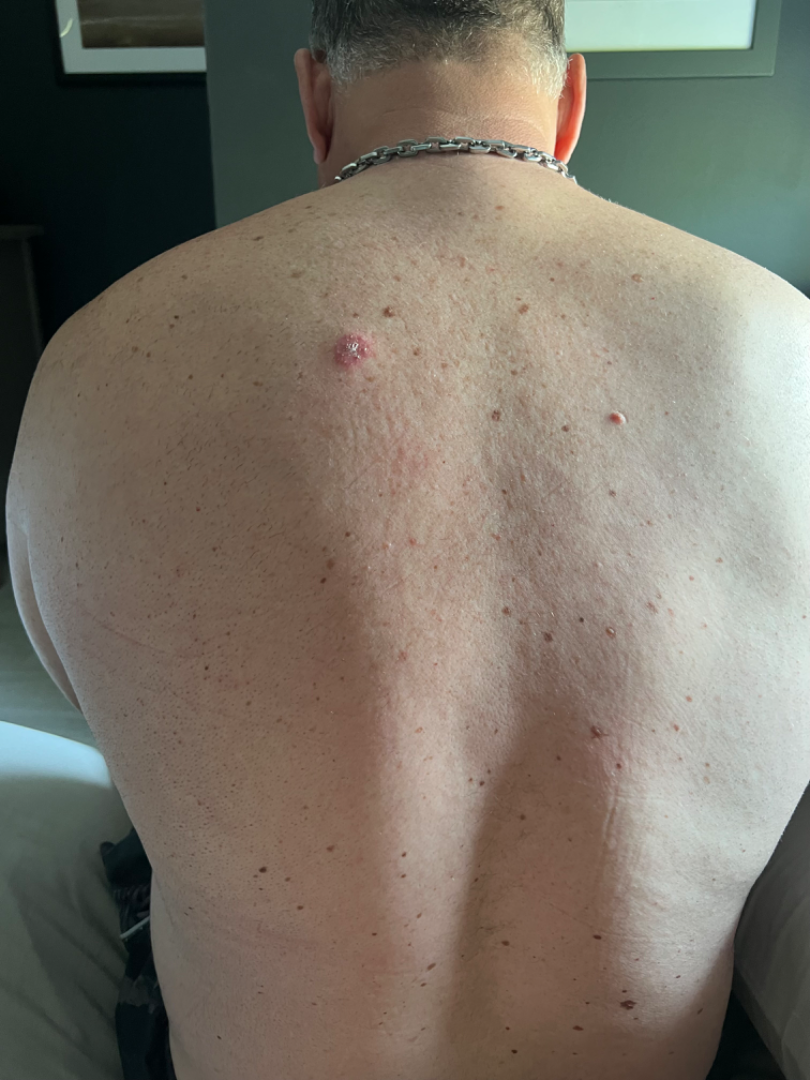Review:
The image was not sufficient for the reviewer to characterize the skin condition.
Patient information:
Close-up view.